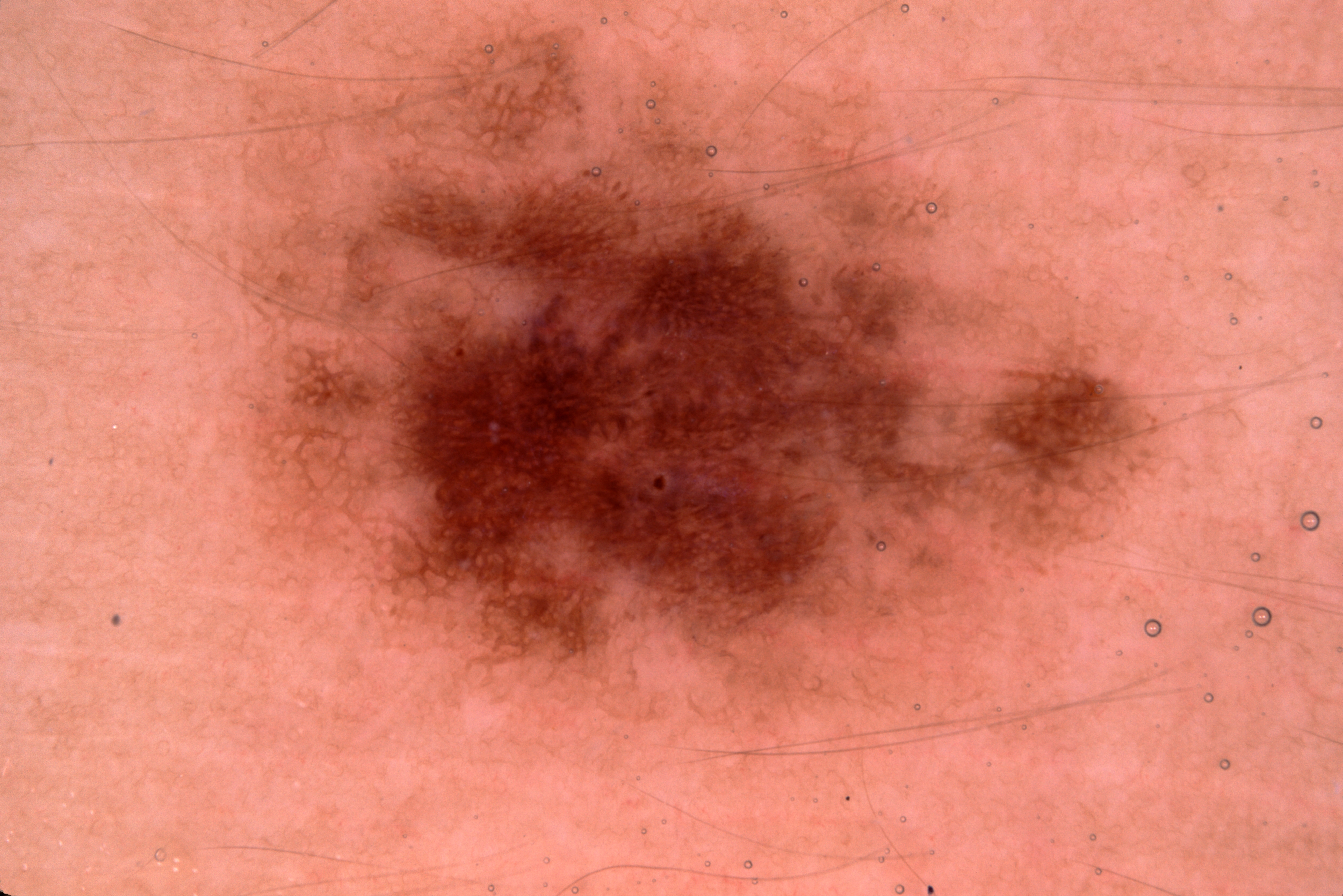Dermoscopy of a skin lesion. The patient is a female aged approximately 30. Dermoscopic review identifies pigment network, with no milia-like cysts, negative network, or streaks. The lesion covers approximately 50% of the dermoscopic field. Lesion location: 211 15 1248 756. Consistent with a melanocytic nevus.